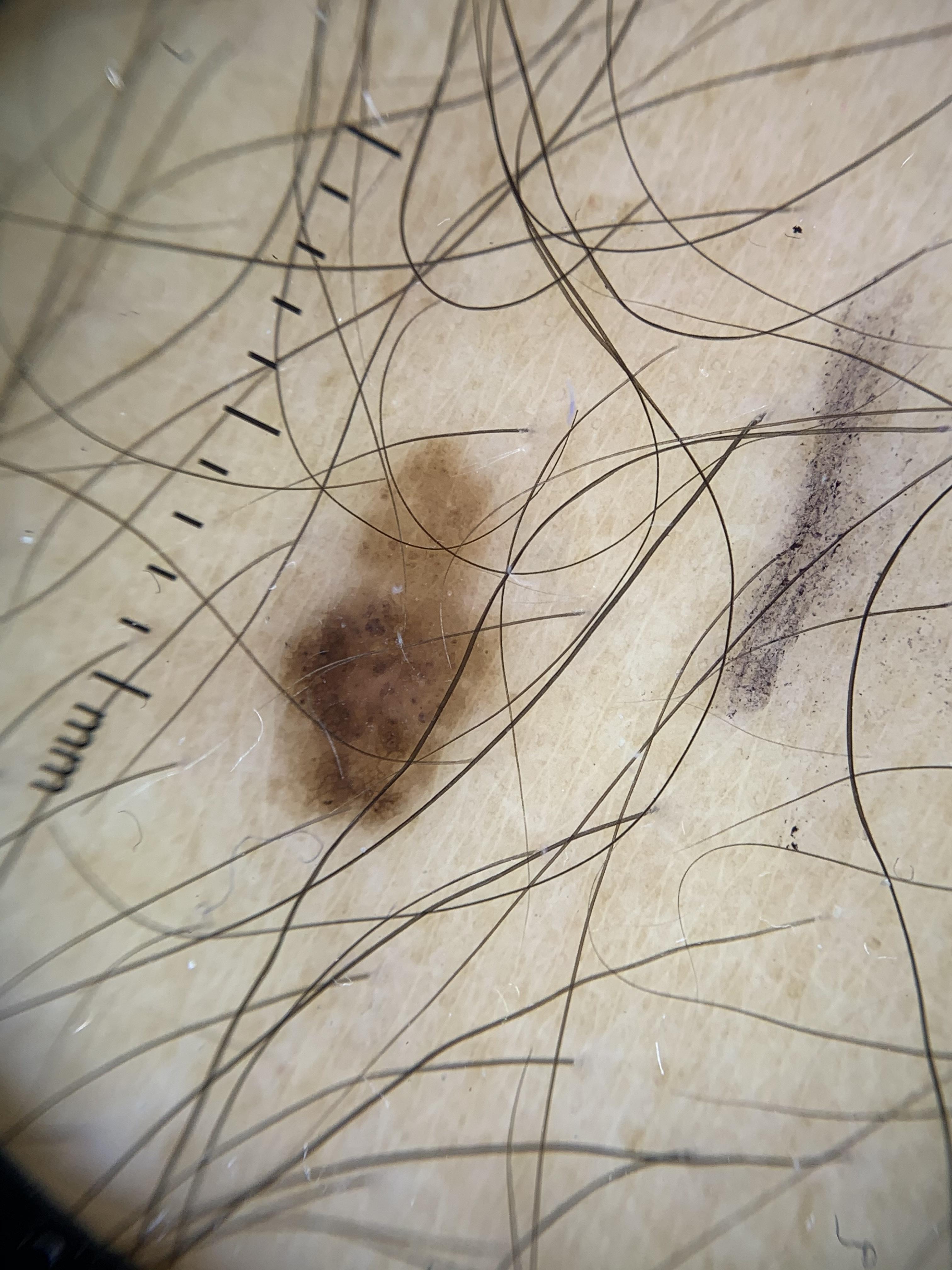A subject aged approximately 50. A contact-polarized dermoscopy image of a skin lesion. The chart notes a first-degree relative with melanoma but no prior melanoma. The lesion was found on the posterior trunk. Biopsy-confirmed as a benign, melanocytic lesion — a nevus.